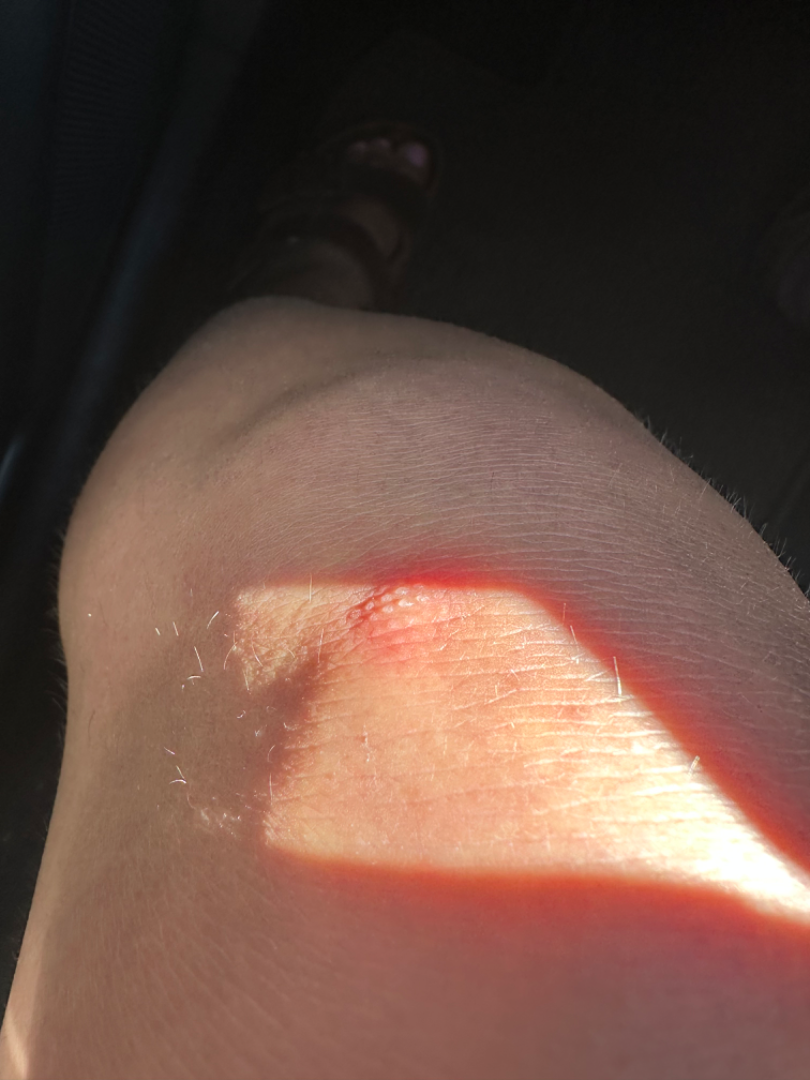Assessment: The reviewing dermatologist was unable to assign a differential diagnosis from the image. Clinical context: An image taken at a distance.